The chart records prior skin cancer (patient or family) and no pesticide exposure · a female subject aged 81 · the patient was assessed as Fitzpatrick I · a smartphone photograph of a skin lesion: 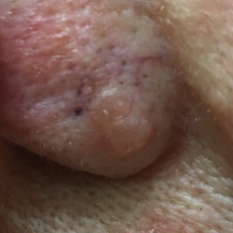The lesion was found on the nose. The lesion measures approximately 5 × 4 mm. The patient reports that the lesion itches, is elevated, and has grown. Histopathological examination showed a basal cell carcinoma.